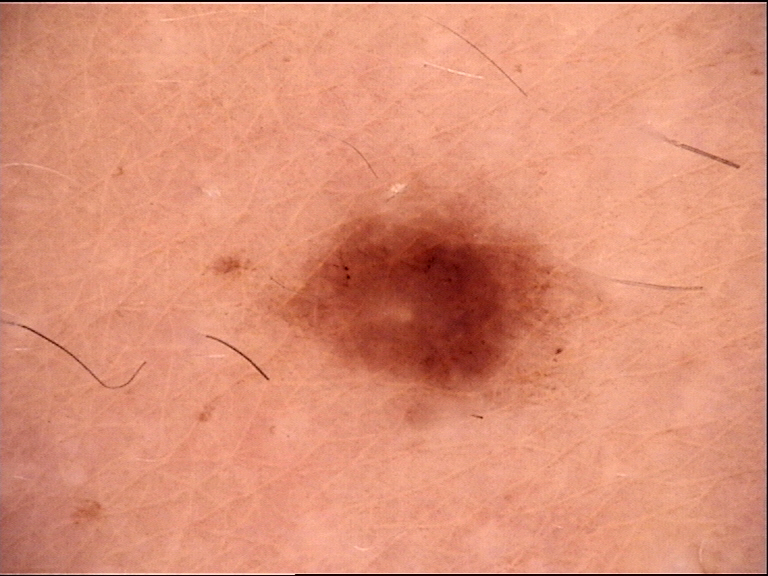• diagnosis — dysplastic junctional nevus (expert consensus)